A clinical close-up of a skin lesion · collected as part of a research study, without a referral diagnosis · the patient says their skin reddens with sun exposure · a female patient 15 years of age · few moles overall by the patient's own estimate · the patient reports no sunbed use:
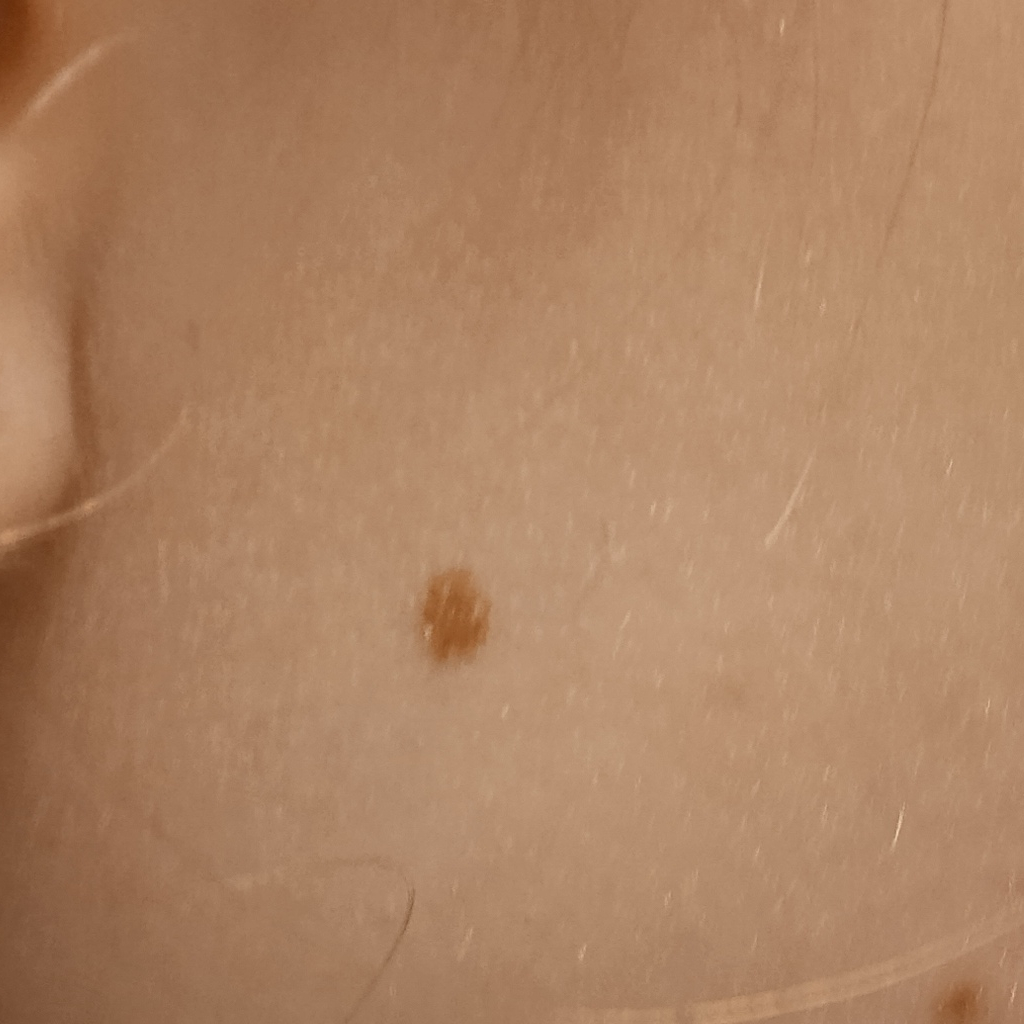Case:
– anatomic site · the face
– size · 3.6 mm
– assessment · melanocytic nevus (dermatologist consensus)